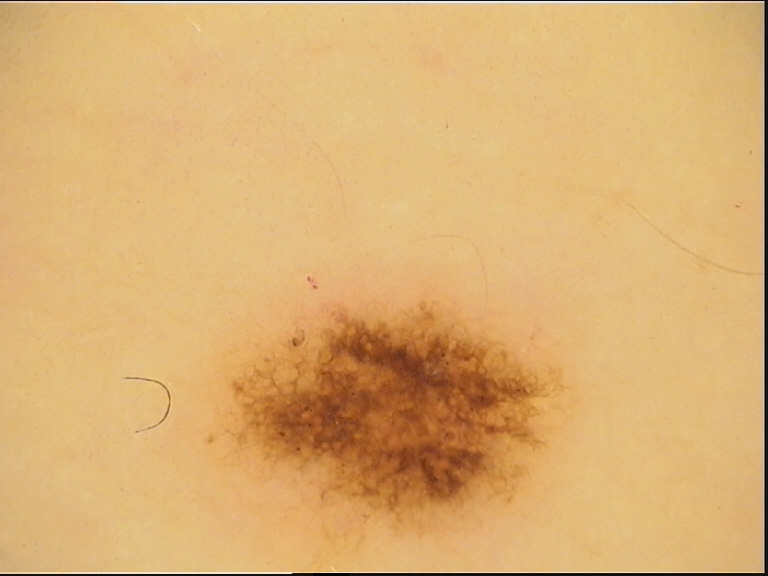Case:
Dermoscopy of a skin lesion.
Impression:
The diagnosis was a dysplastic junctional nevus.